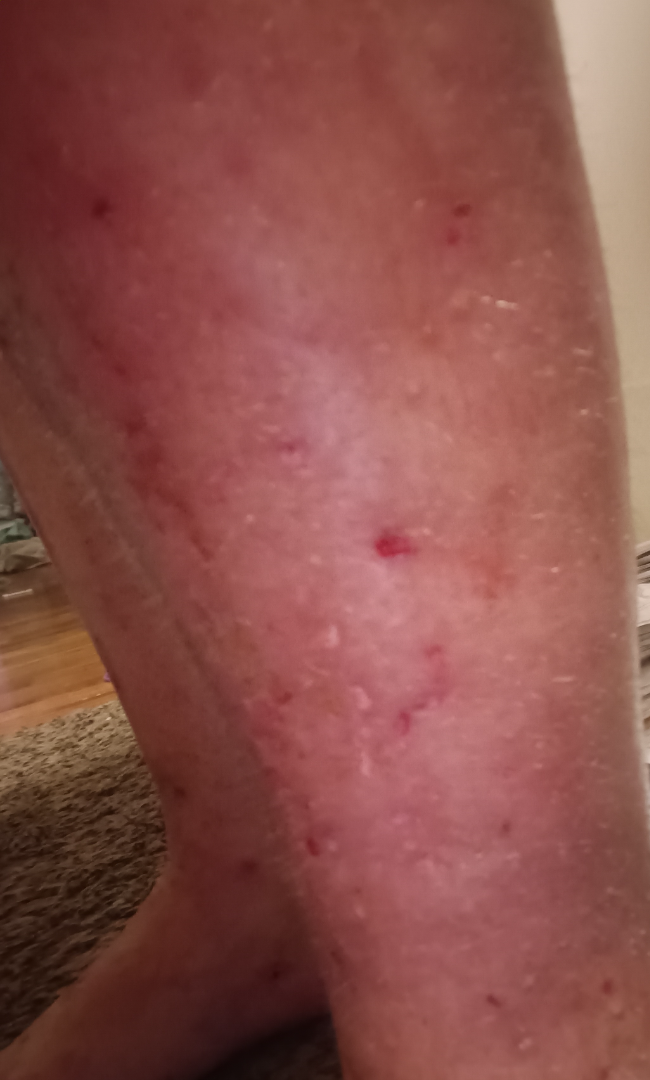• dermatologist impression · the favored diagnosis is Stasis Dermatitis; the differential also includes Cellulitis; also consider Eczema